A dermoscopy image of a single skin lesion.
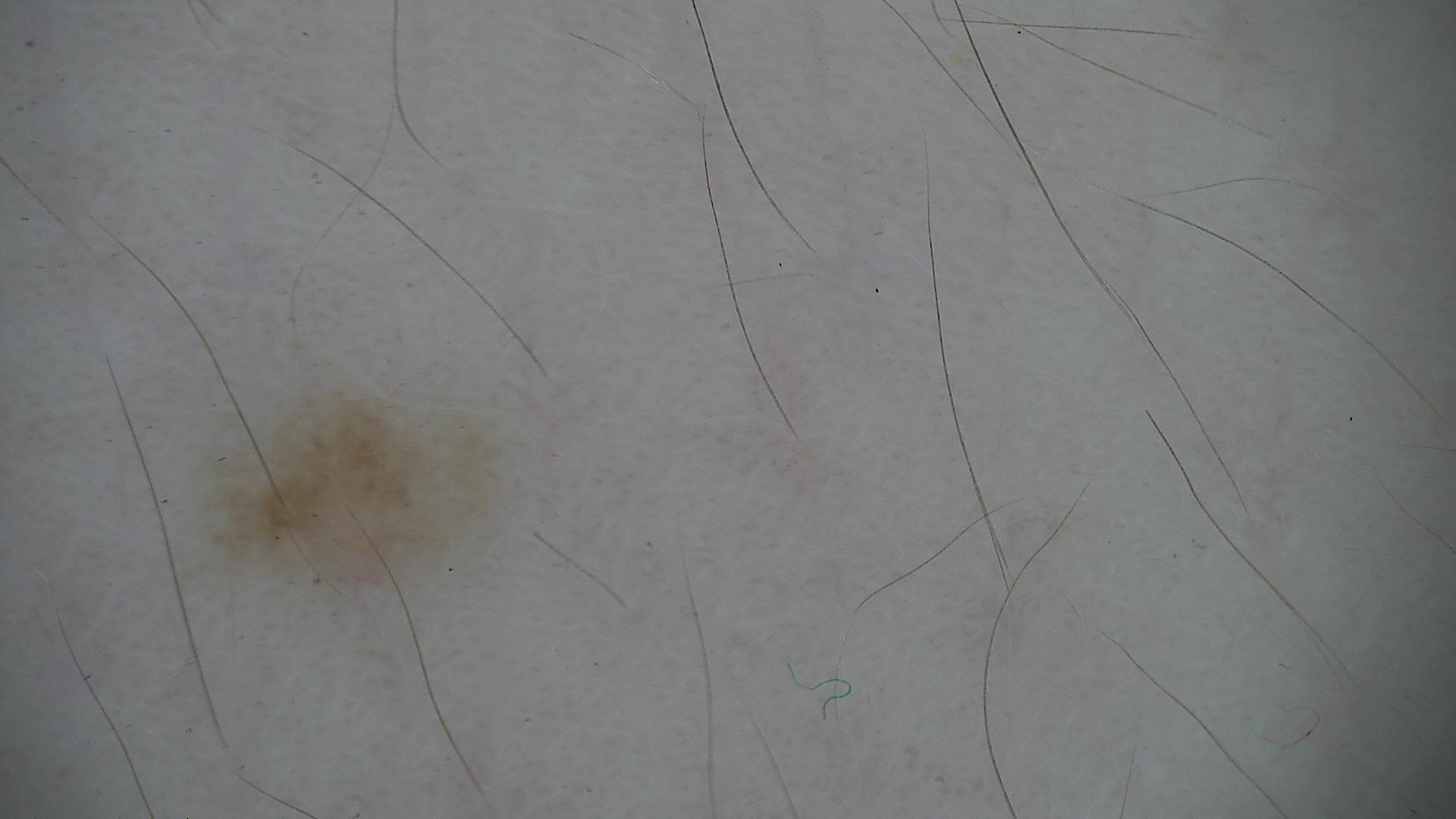assessment = dysplastic junctional nevus (expert consensus).